Present for less than one week; symptoms reported: itching; texture is reported as raised or bumpy; close-up view; the affected area is the leg — 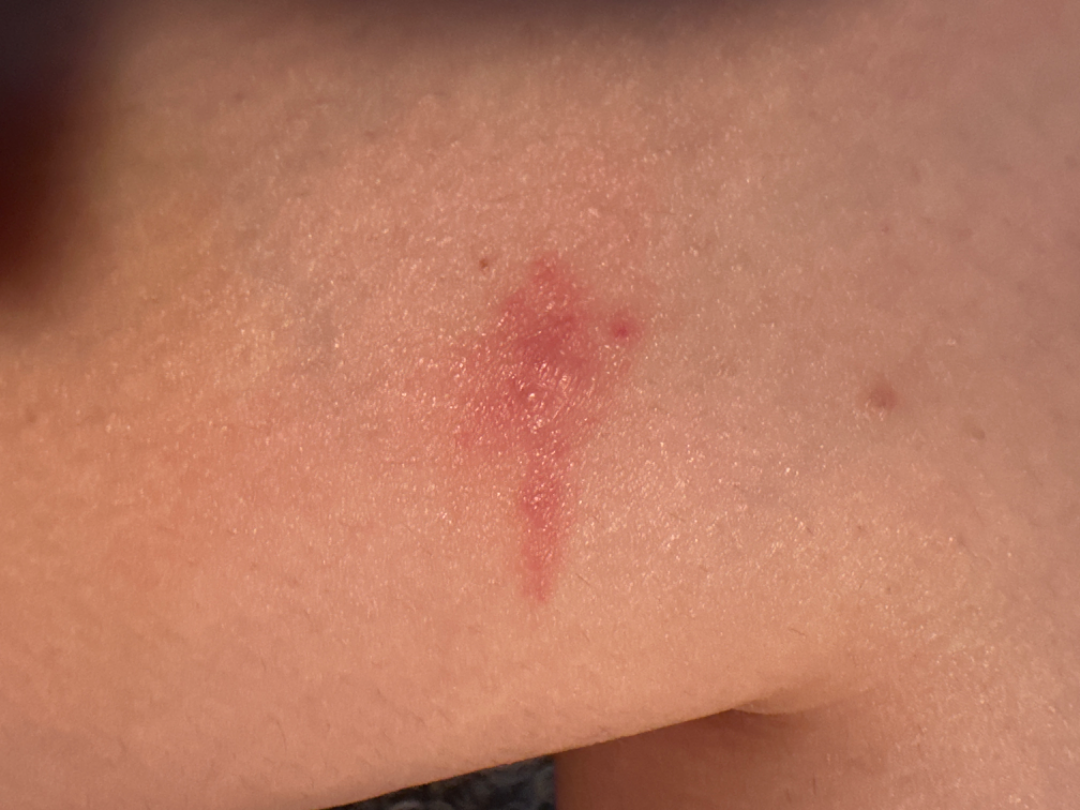Assessment: The reviewing dermatologist was unable to assign a differential diagnosis from the image.